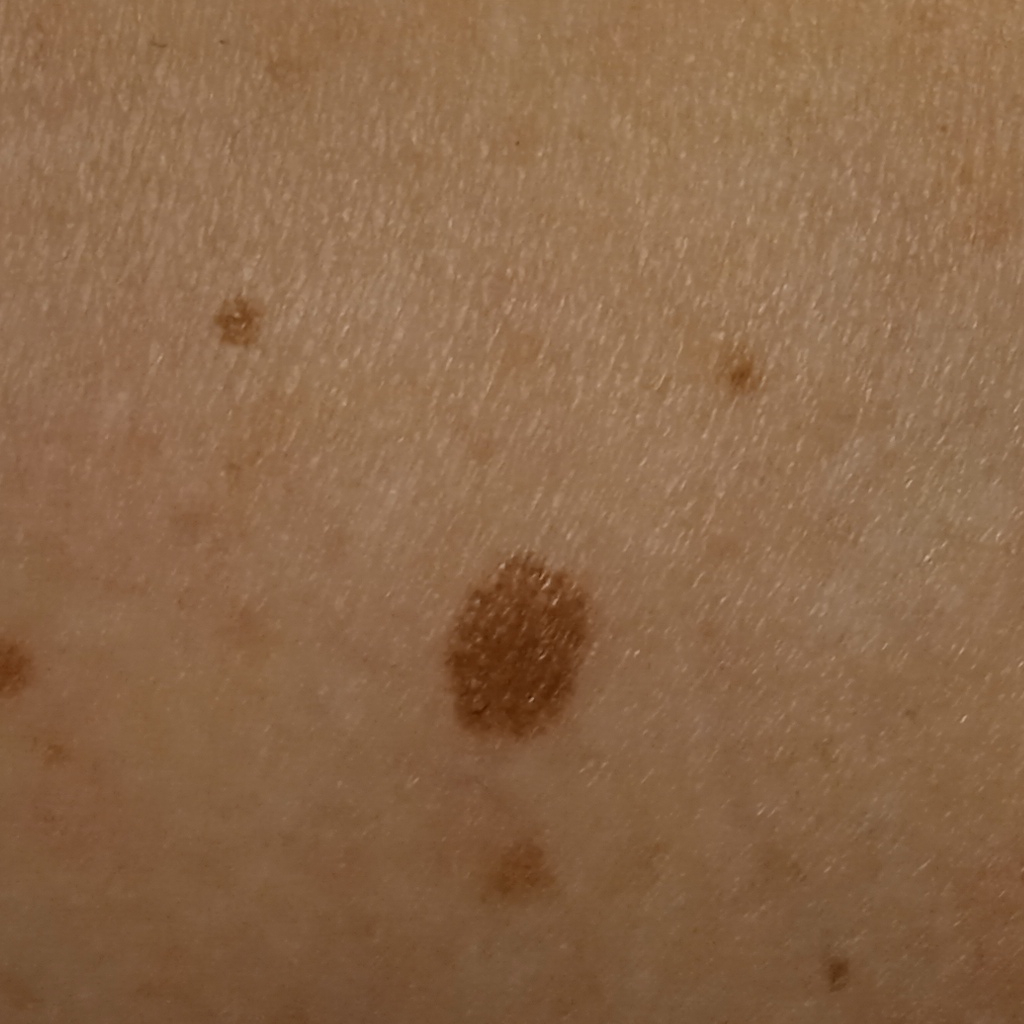Referred for assessment of suspected melanocytic nevus. A female subject aged 59. A moderate number of moles by the patient's own estimate. The lesion is on an arm. The lesion measures approximately 6.7 mm. Histopathology confirmed an atypical (dysplastic) nevus, following excision.